A dermoscopic close-up of a skin lesion:
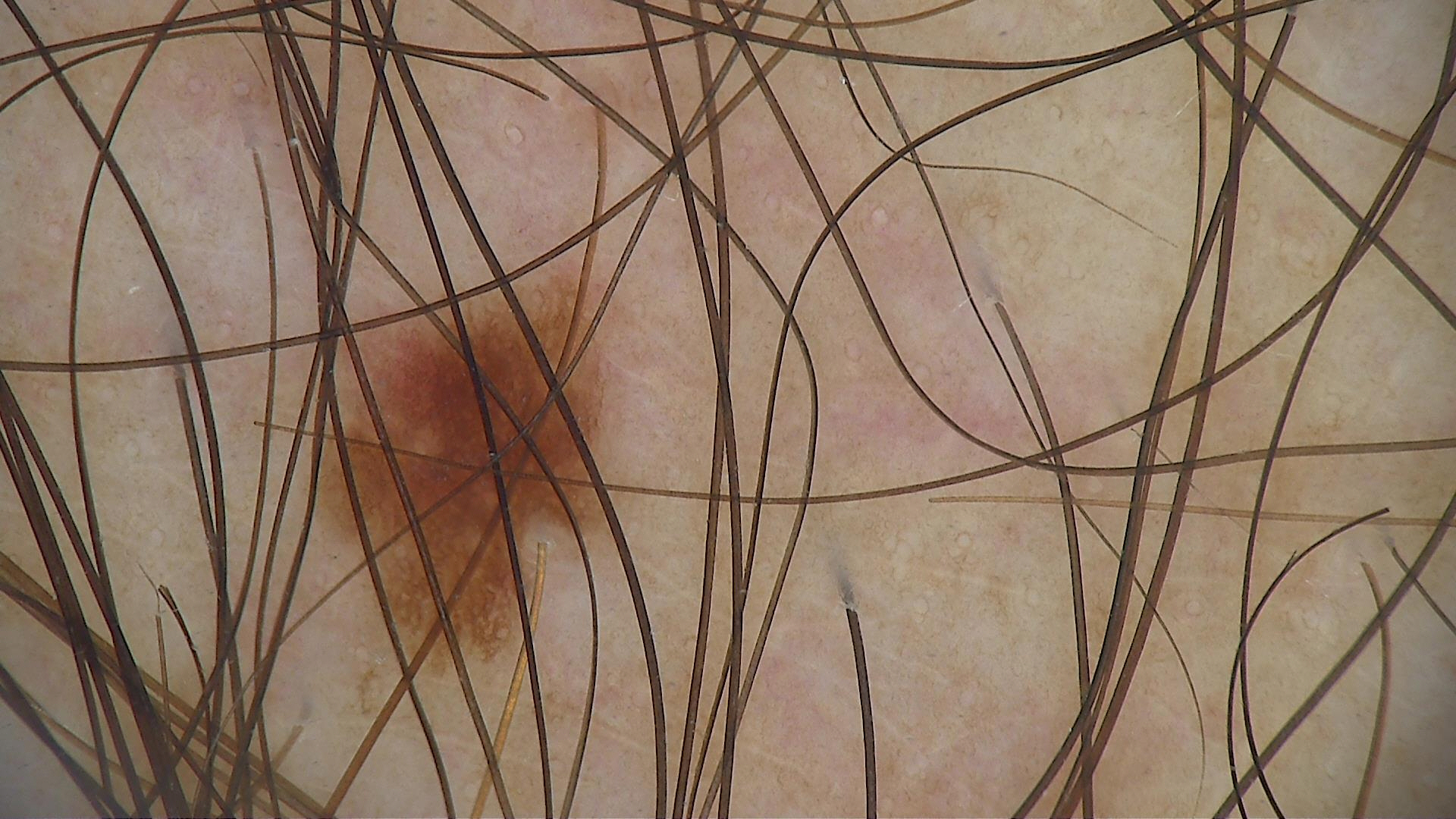Consistent with a dysplastic junctional nevus.